The lesion is described as raised or bumpy. The patient described the issue as a rash. A close-up photograph. Skin tone: Fitzpatrick phototype II. Present for one to three months. The lesion involves the arm — 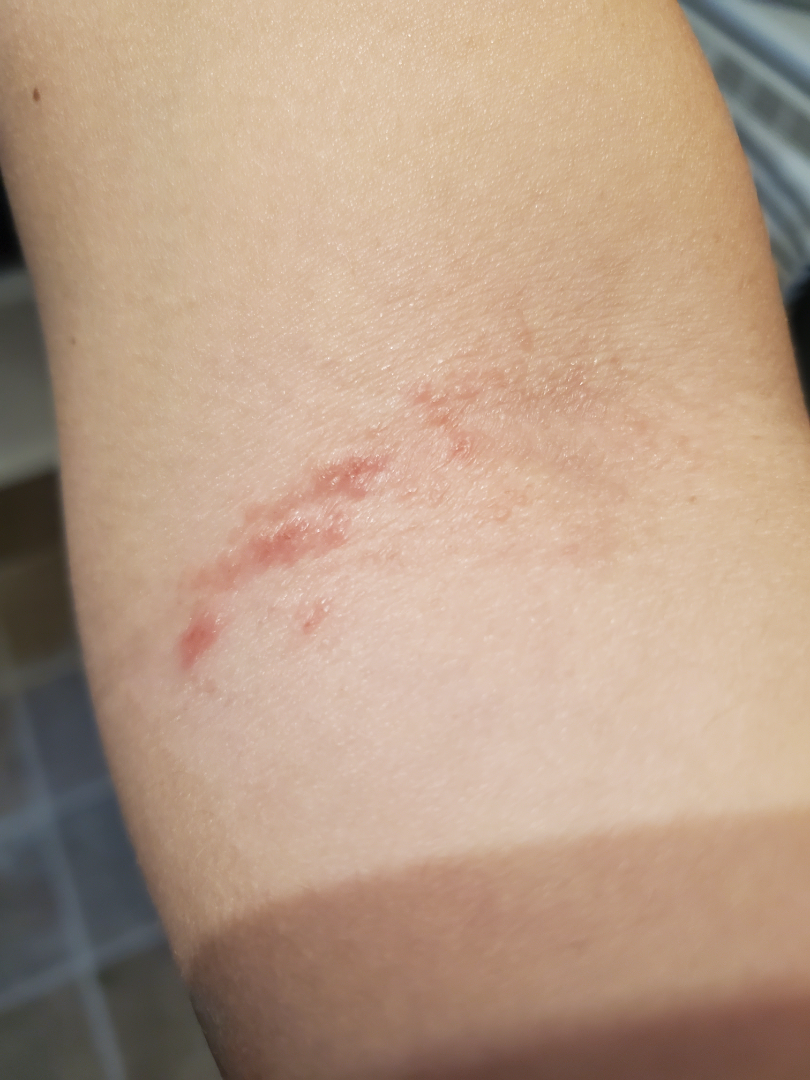The reviewing dermatologist's impression was: Eczema (0.54); Tinea (0.23); Allergic Contact Dermatitis (0.23).